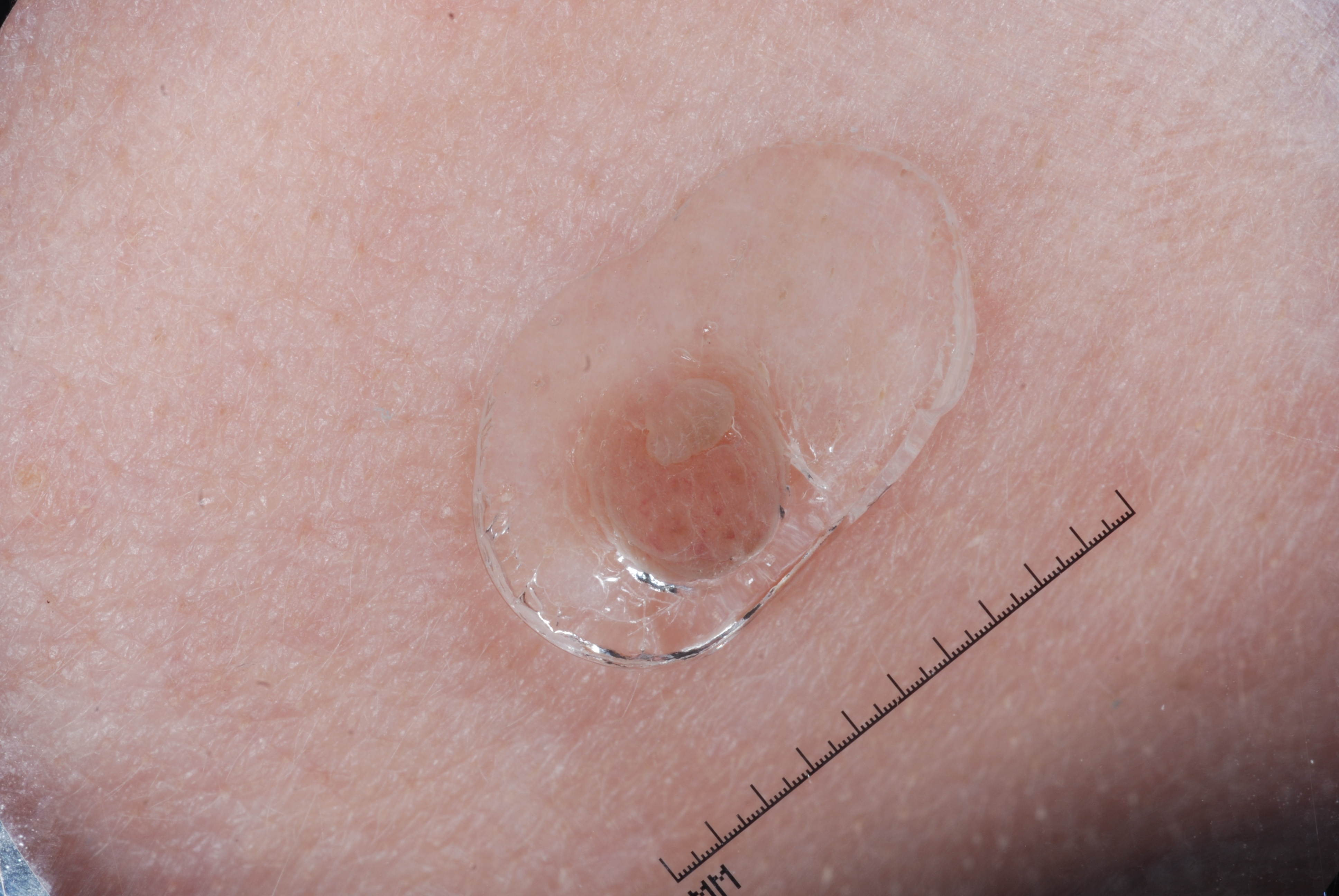A female patient aged approximately 45.
A dermoscopic close-up of a skin lesion.
On dermoscopy, the lesion shows no negative network, pigment network, milia-like cysts, or streaks.
With coordinates (x1, y1, x2, y2), lesion location: bbox=[575, 365, 784, 560].
Expert review diagnosed this as a melanocytic nevus.